A dermoscopic close-up of a skin lesion:
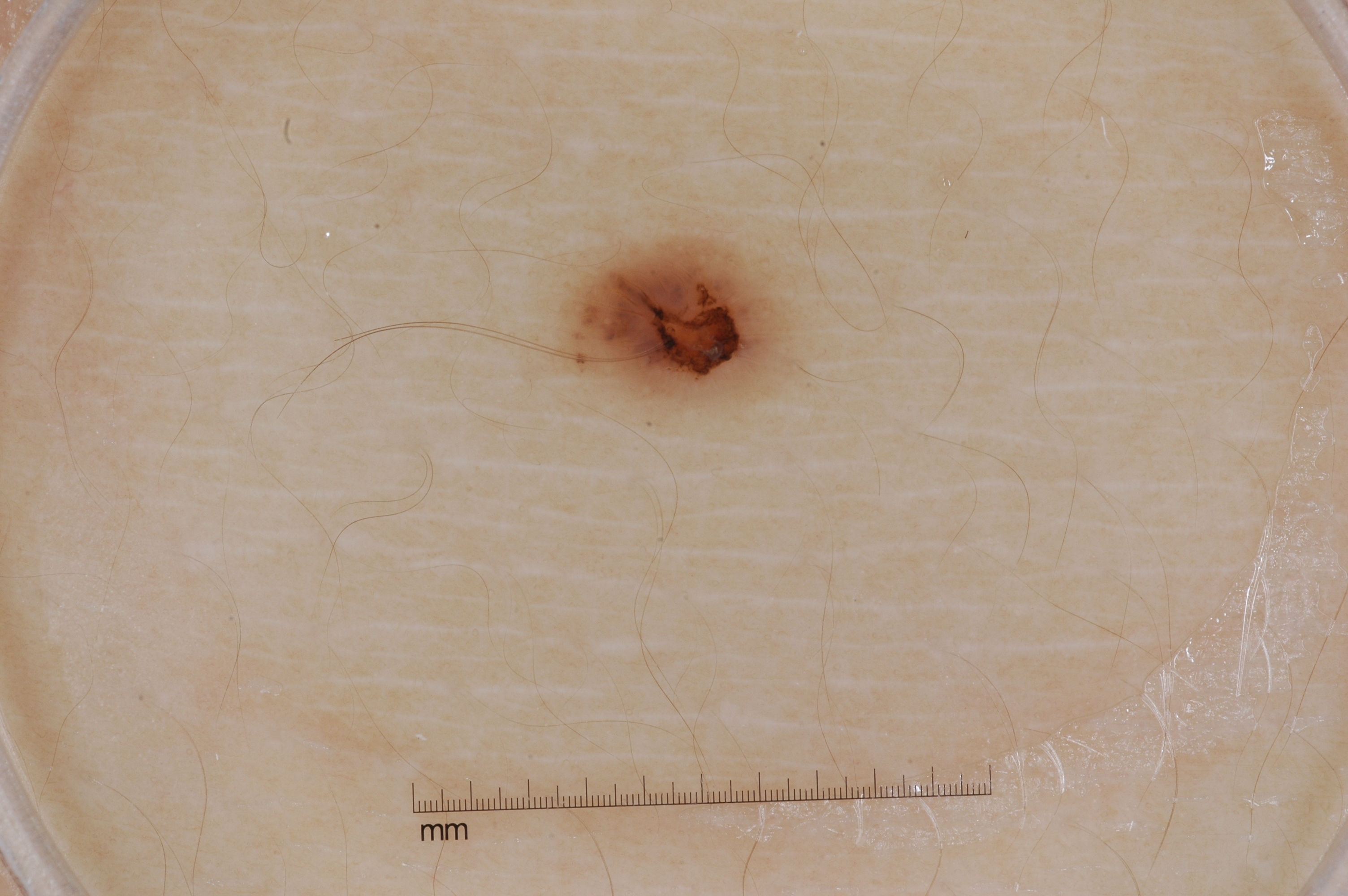| field | value |
|---|---|
| location | x1=548, y1=224, x2=801, y2=413 |
| absent dermoscopic findings | pigment network, milia-like cysts, streaks, and negative network |
| diagnostic label | a melanocytic nevus, a benign lesion |